The lesion is associated with burning, enlargement, itching, pain and bothersome appearance · lay graders estimated 3 on the Monk skin tone scale · female subject, age 30–39 · the patient considered this a rash · the photograph is a close-up of the affected area · the patient reports the condition has been present for less than one week · located on the back of the hand, leg and arm · the patient reports the lesion is fluid-filled and raised or bumpy — 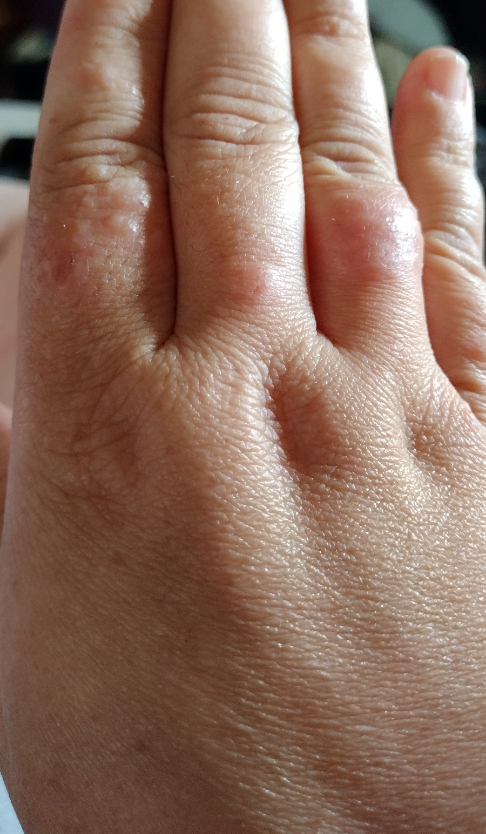{"assessment": "unable to determine"}